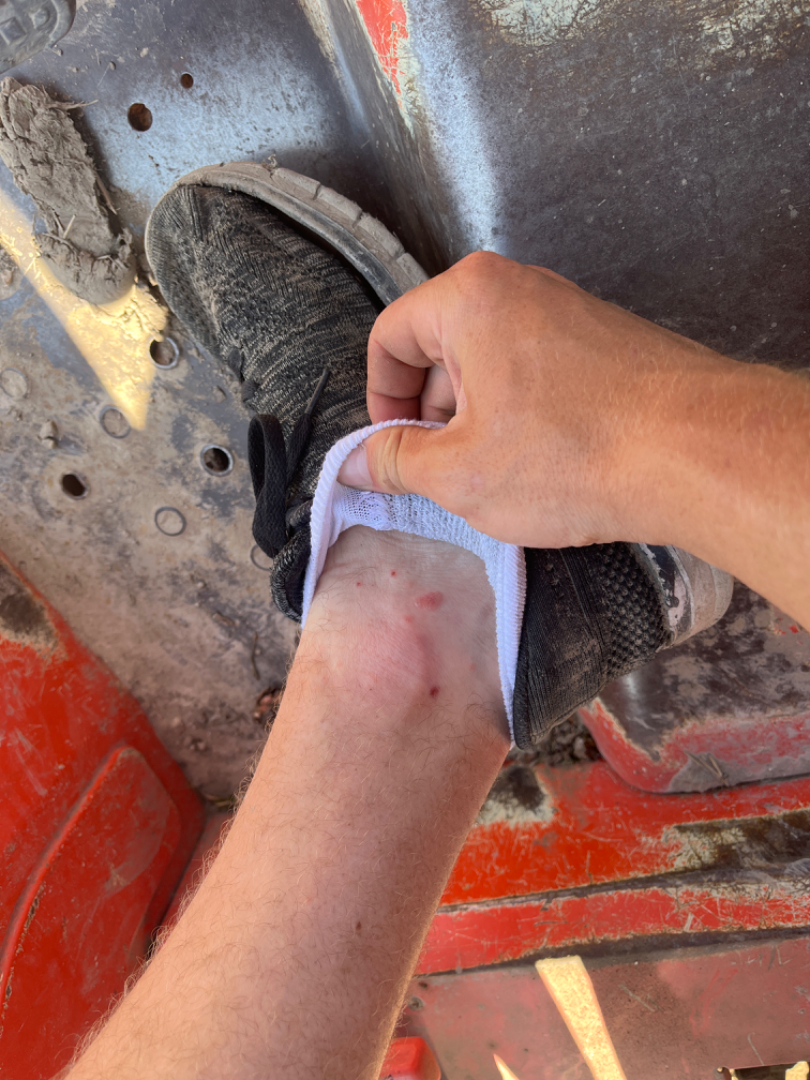Q: Could the case be diagnosed?
A: indeterminate from the photograph
Q: Image view?
A: at a distance